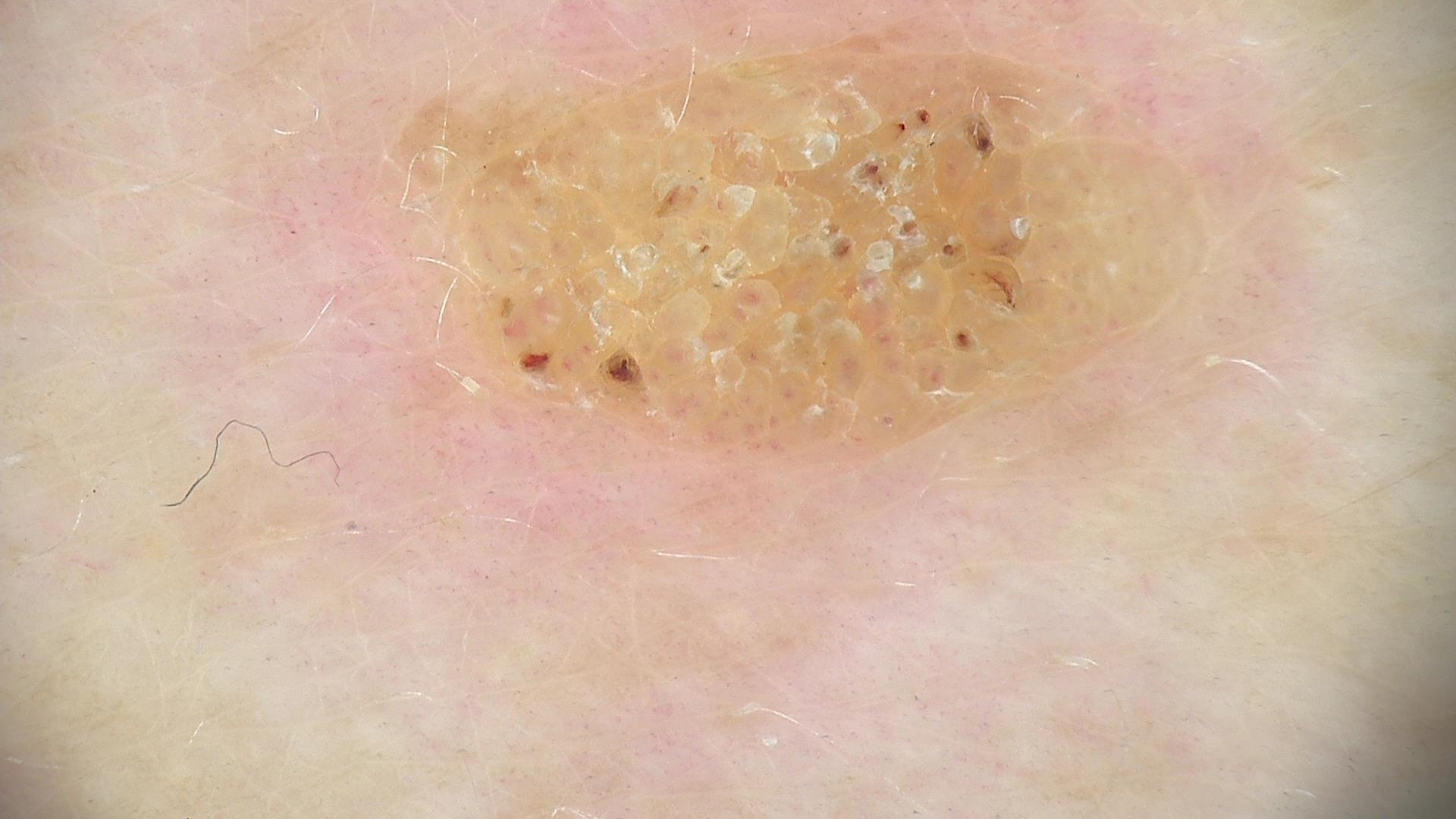| feature | finding |
|---|---|
| diagnosis | seborrheic keratosis (expert consensus) |